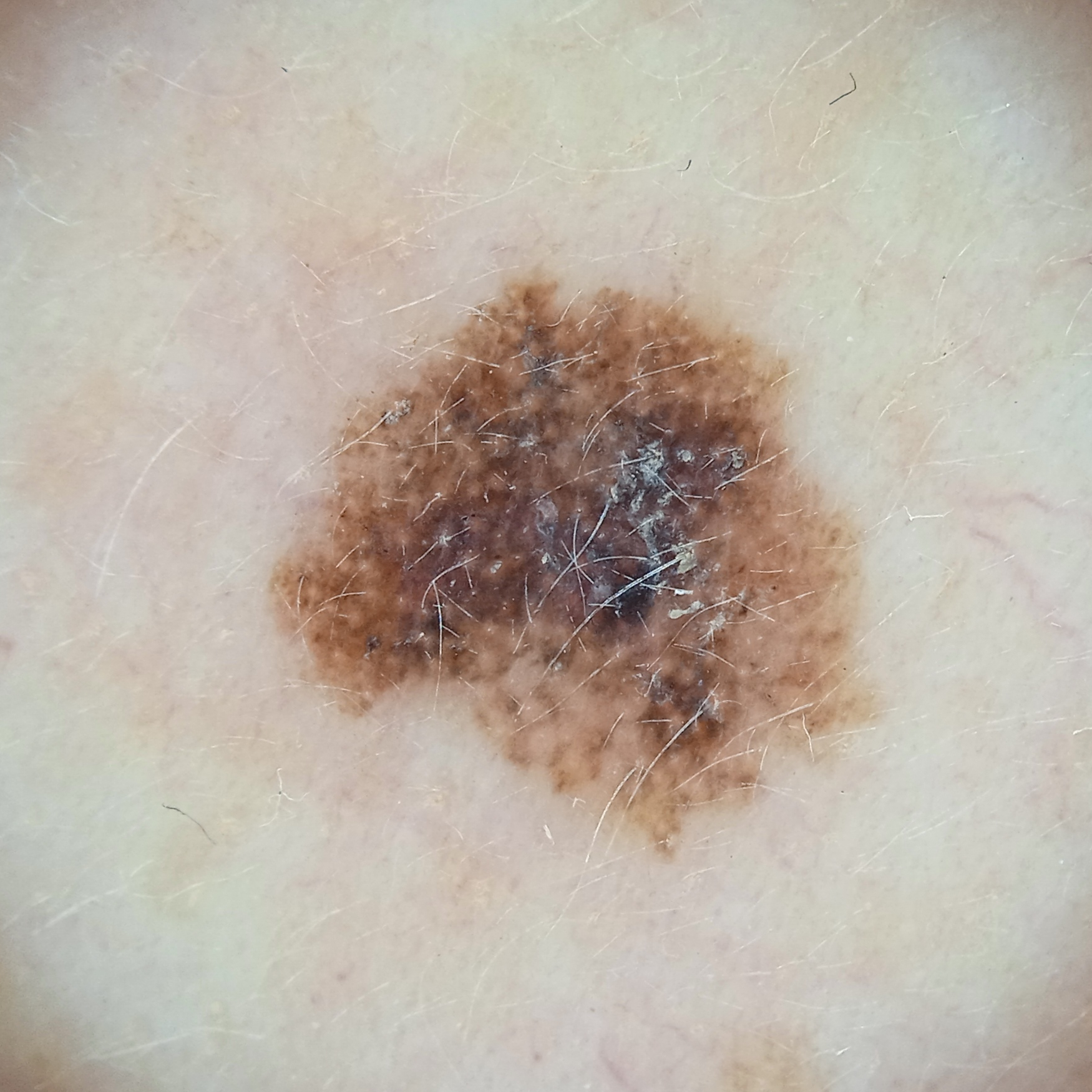The patient says their skin reddens with sun exposure. A female subject aged 50. The patient describes having a moderate number of moles. A dermoscopic image of a skin lesion. Located on the face. Measuring roughly 7 mm. The biopsy diagnosis was a melanoma, following excision, with a Breslow thickness of 0.4 mm.